The photograph is a close-up of the affected area — 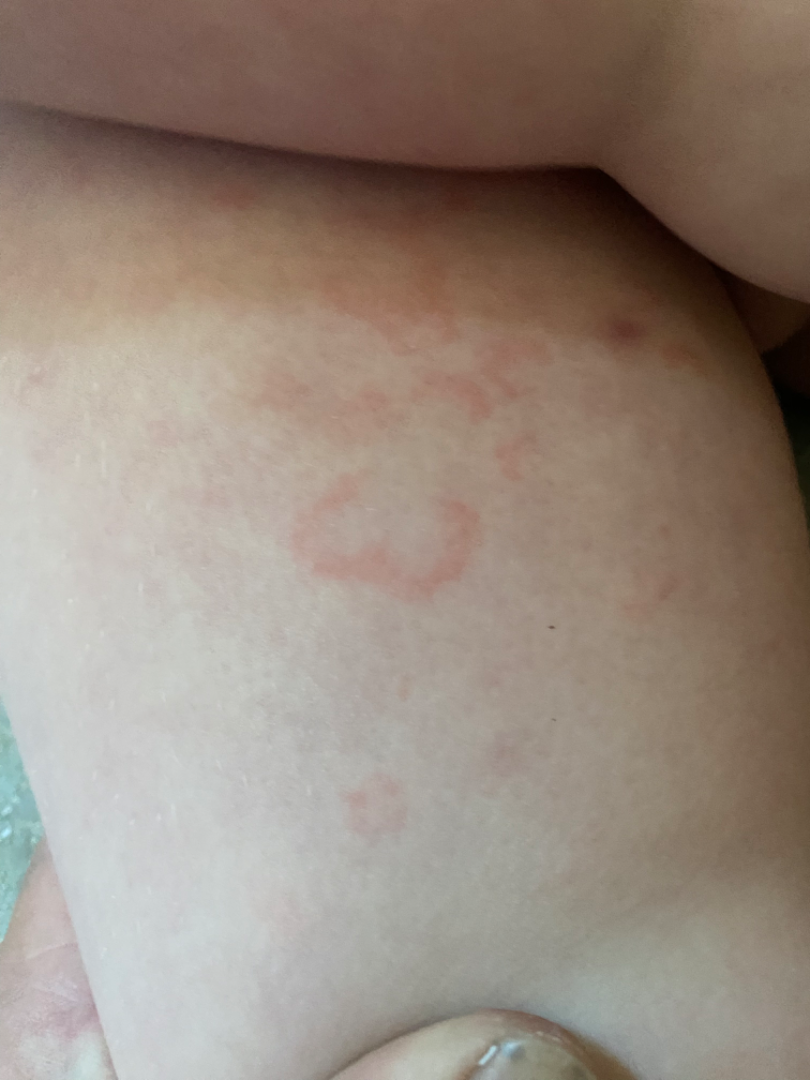The reviewing dermatologist was unable to assign a differential diagnosis from the image.